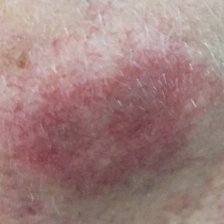skin type = II | imaging = clinical photograph | patient = male, 58 years old | exposures = no prior skin cancer (patient or family) | body site = the face | lesion diameter = 8 × 5 mm | symptoms = elevation | diagnostic label = basal cell carcinoma (biopsy-proven).